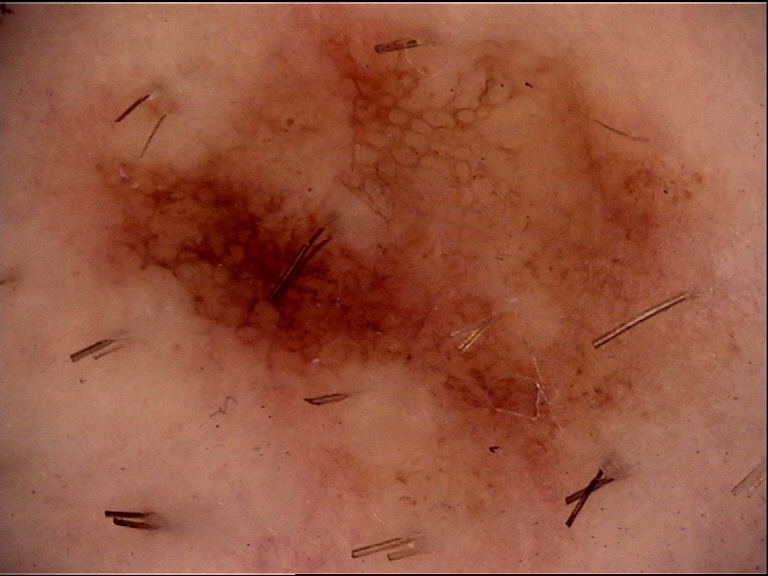label = dysplastic junctional nevus (expert consensus)